A dermoscopy image of a single skin lesion.
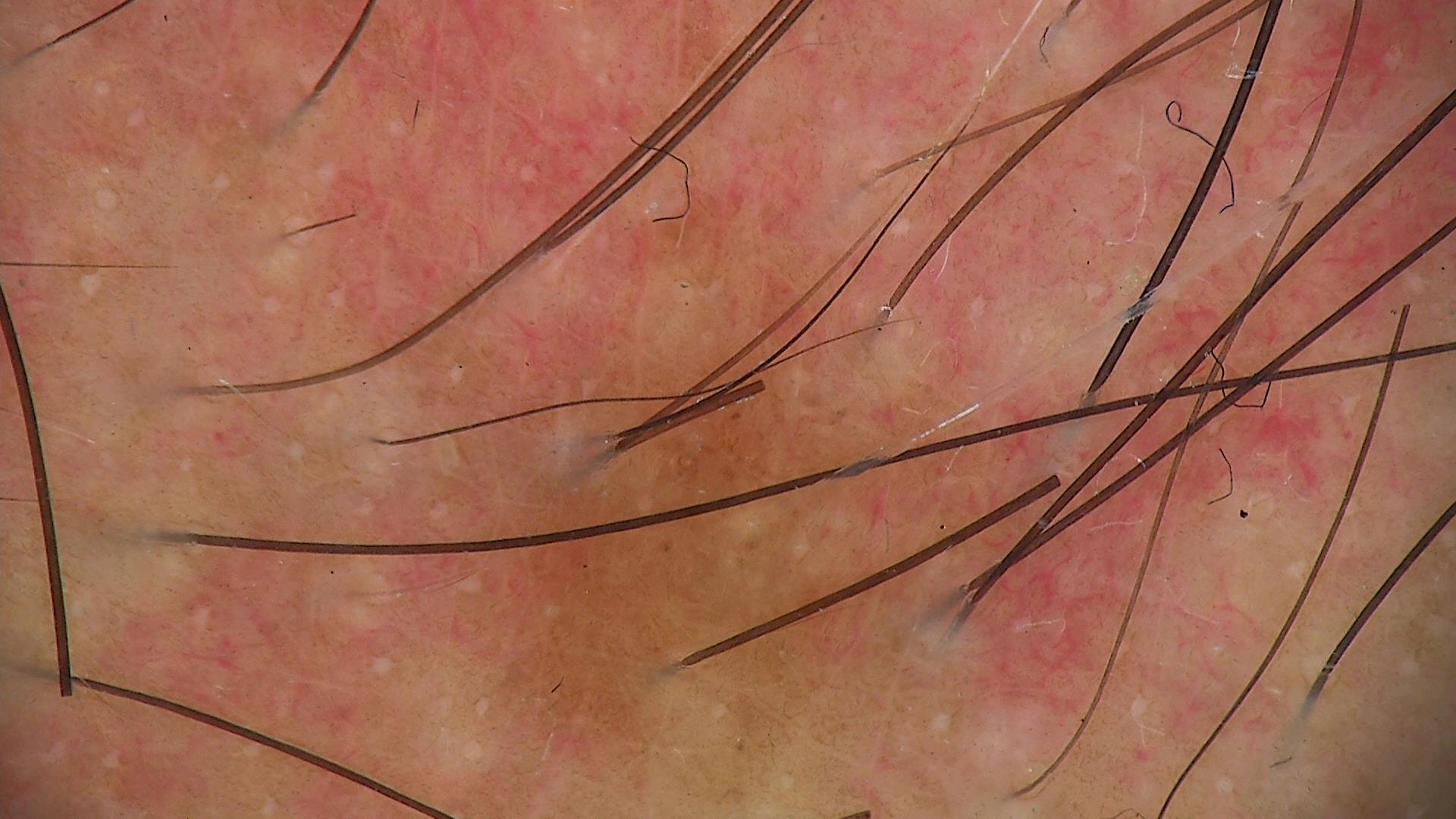assessment: dysplastic junctional nevus (expert consensus)